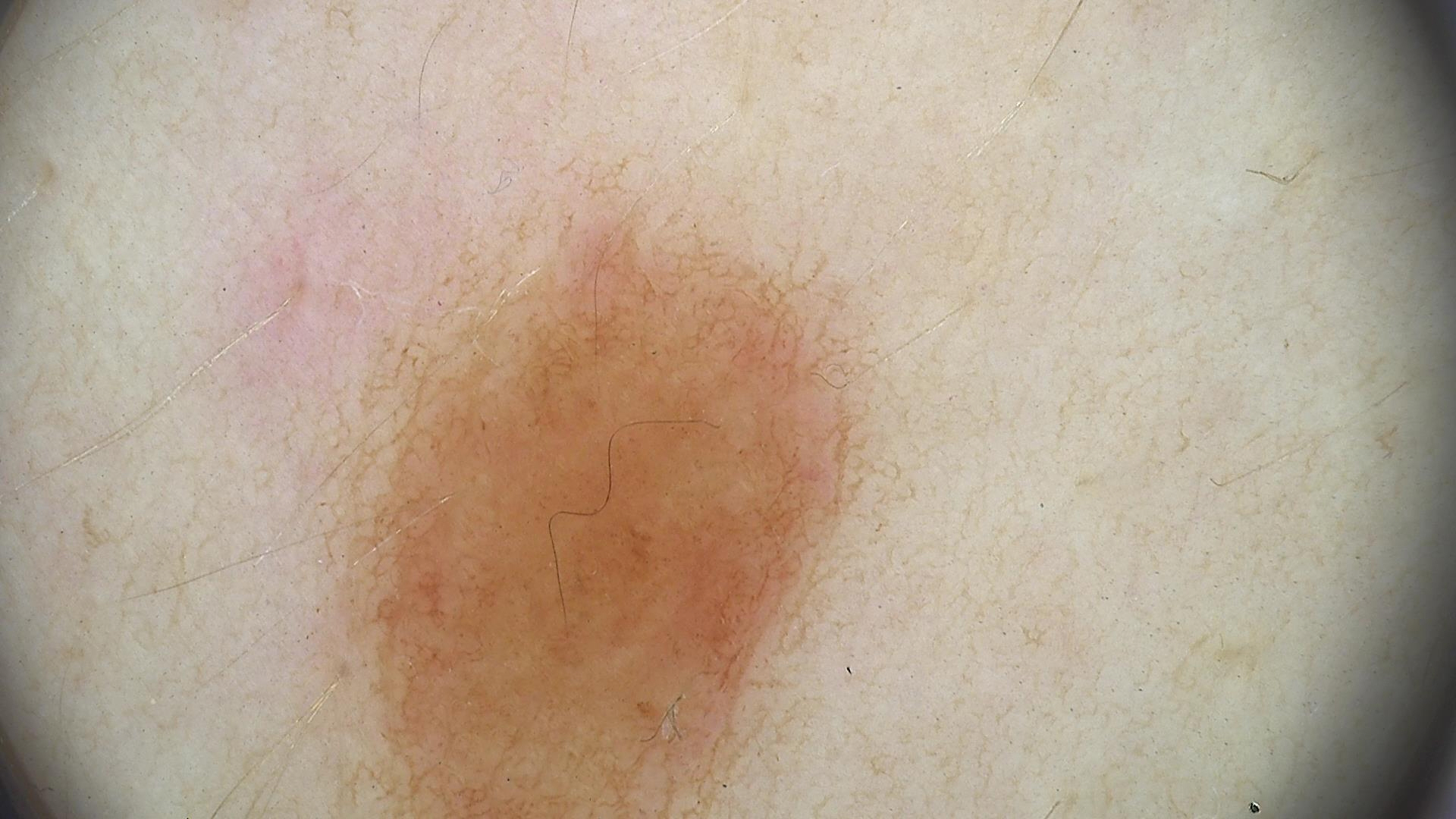A dermoscopic image of a skin lesion.
Consistent with a benign lesion — a dysplastic junctional nevus.